An image taken at a distance. The affected area is the back of the torso, head or neck and front of the torso.
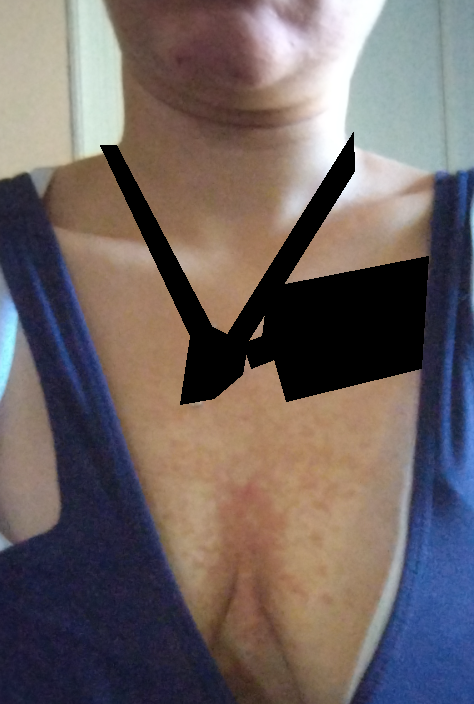No differential diagnosis could be assigned on photographic review.